An overview clinical photograph of a skin lesion:
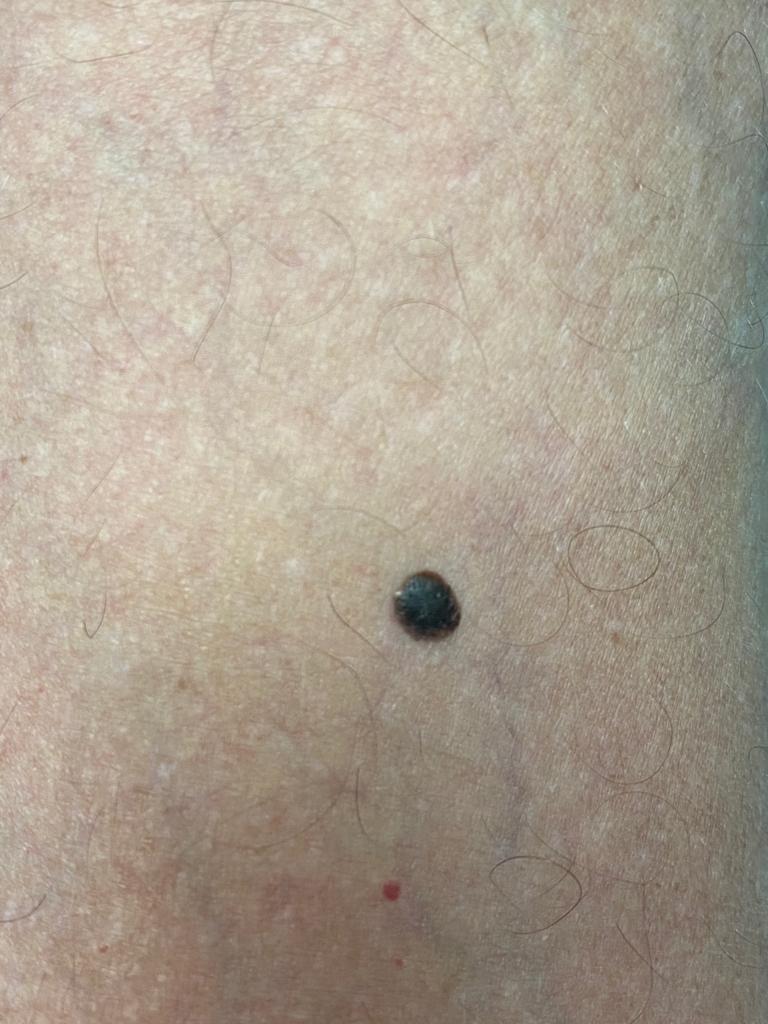anatomic site=the trunk (the posterior trunk); assessment=Seborrheic keratosis.